A female patient roughly 60 years of age · a dermoscopic view of a skin lesion: 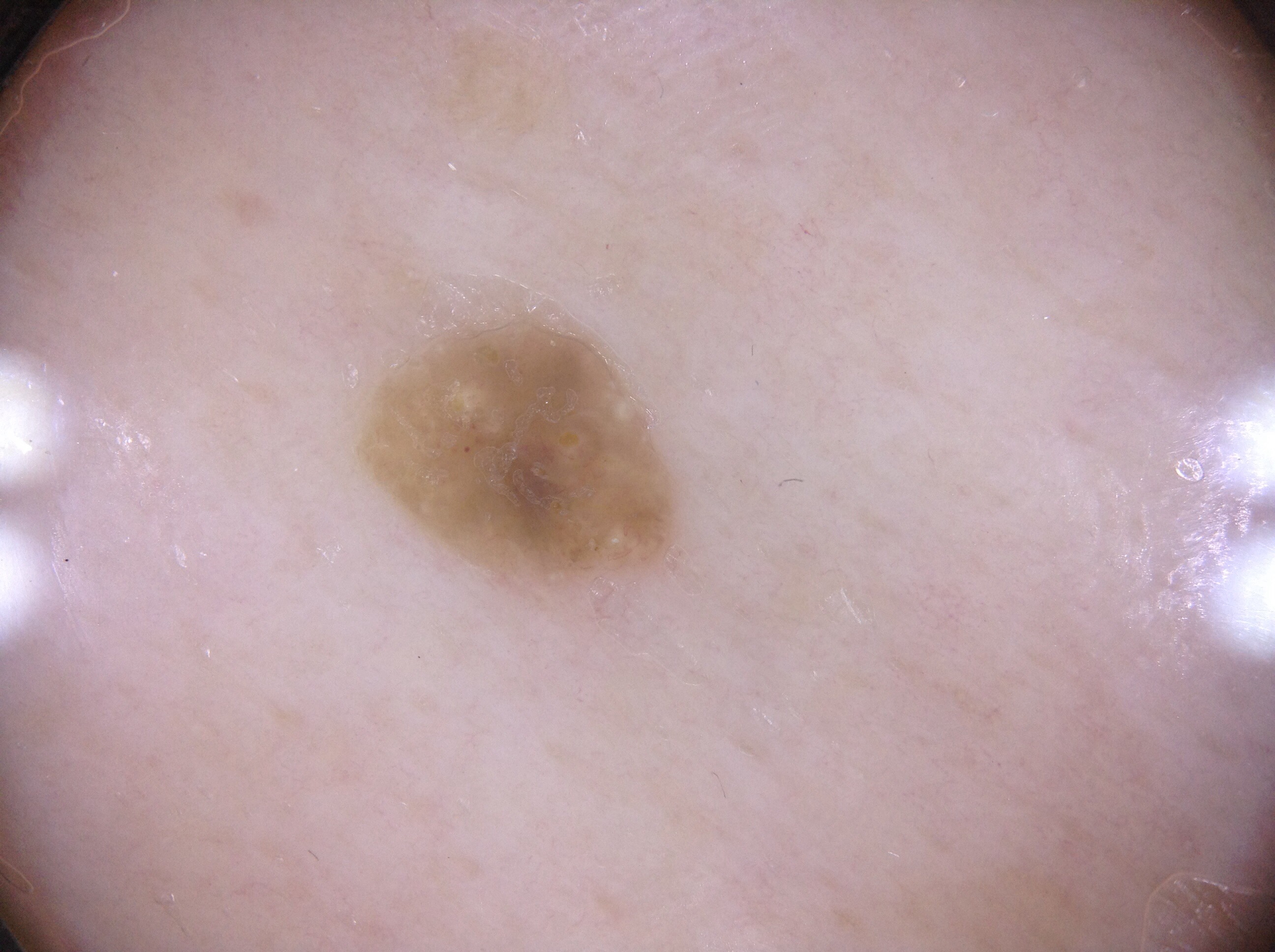lesion location = [369, 320, 677, 580]
extent = small
dermoscopic features = milia-like cysts; absent: pigment network, negative network, and streaks
diagnostic label = a seborrheic keratosis, a benign lesion